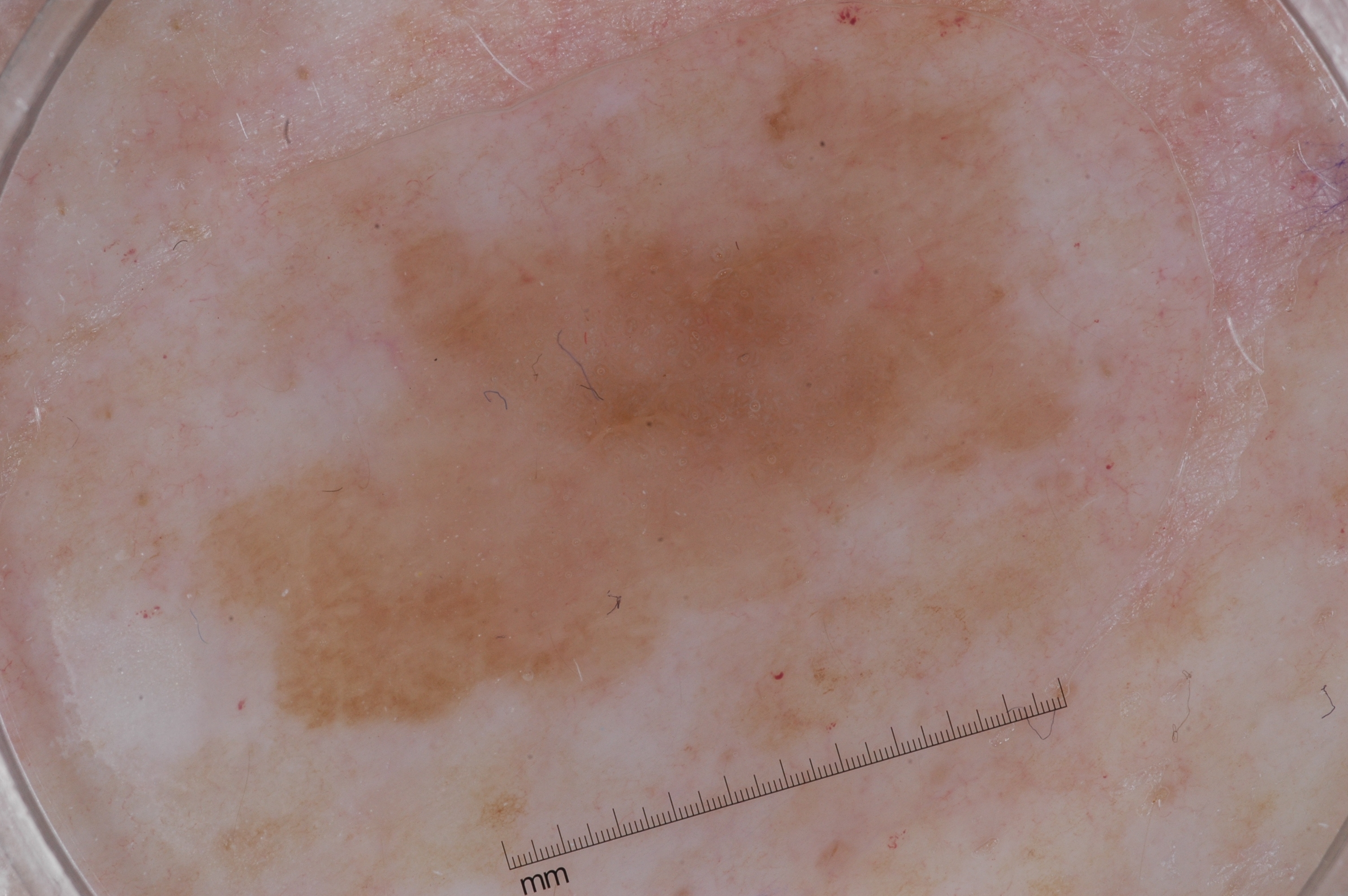| feature | finding |
|---|---|
| patient | female, roughly 55 years of age |
| modality | dermatoscopic image of a skin lesion |
| dermoscopic pattern | milia-like cysts; absent: negative network, streaks, and pigment network |
| size | large |
| bounding box | bbox(201, 56, 1074, 728) |
| assessment | a seborrheic keratosis |